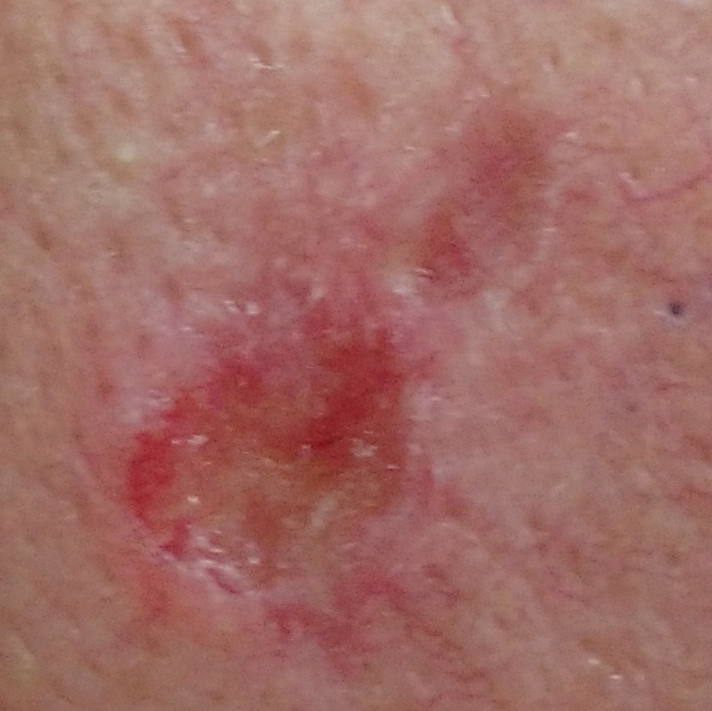Notes:
• exposure history — prior malignancy (patient or family), pesticide exposure, prior skin cancer (patient or family)
• FST — II
• image type — clinical photo
• patient — female, in their early 70s
• body site — the face
• lesion diameter — 17x9 mm
• patient-reported symptoms — pain, bleeding, elevation, itching
• diagnosis — basal cell carcinoma (biopsy-proven)